An image taken at an angle:
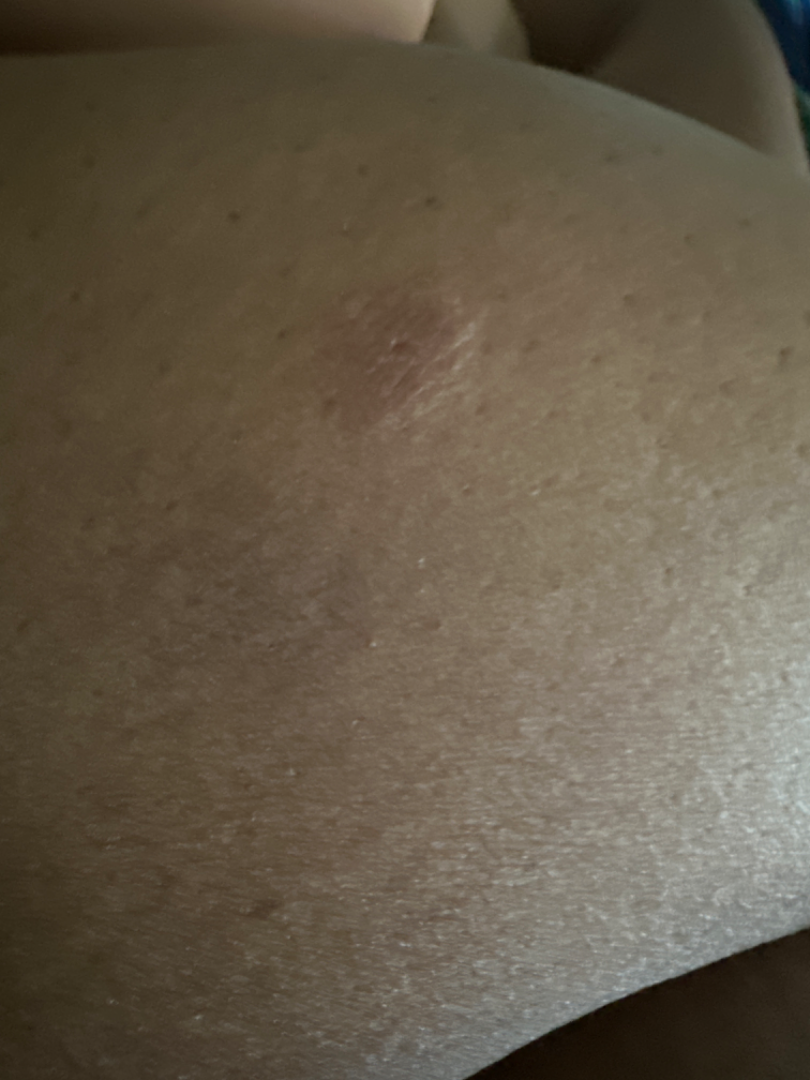Assessment:
The case was difficult to assess from the available photograph.
Clinical context:
Reported duration is one to four weeks. No relevant systemic symptoms. The lesion is associated with darkening and enlargement. The contributor reports the lesion is raised or bumpy and rough or flaky.